The patient is male; close-up view; the arm, back of the hand and back of the torso are involved:
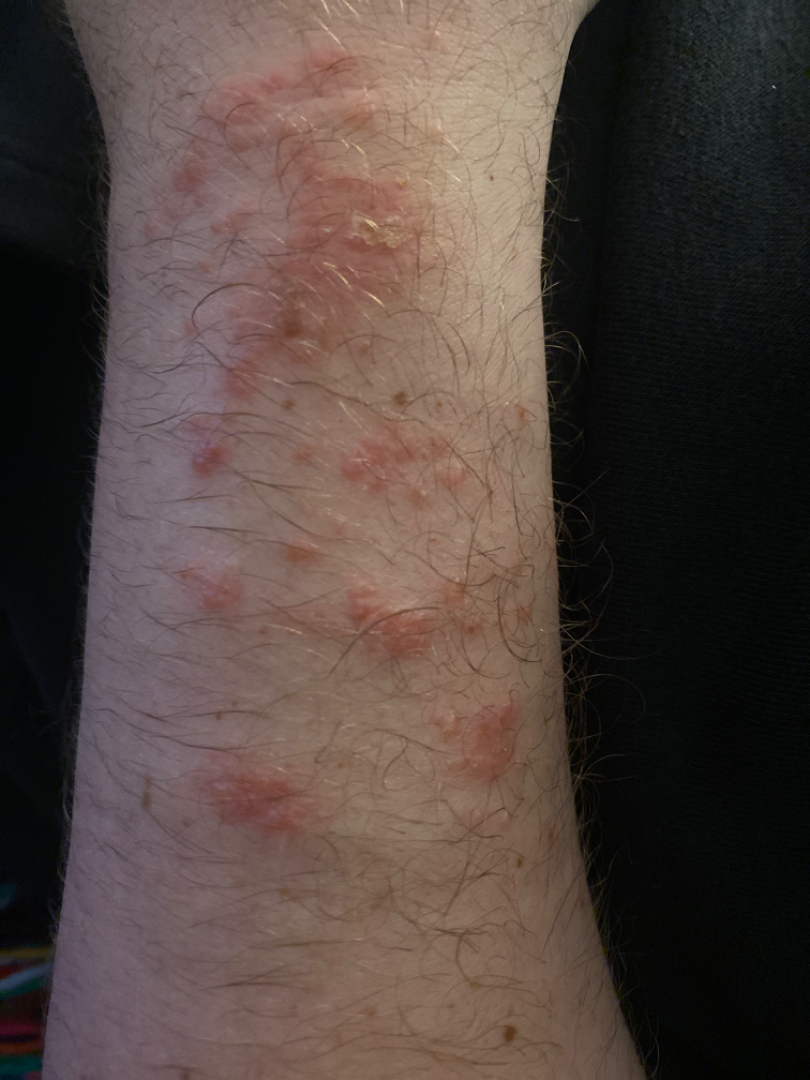<case>
<differential>
  <leading>Allergic Contact Dermatitis</leading>
  <considered>Impetigo, Eczema</considered>
</differential>
</case>